A dermoscopic close-up of a skin lesion. A female subject approximately 35 years of age:
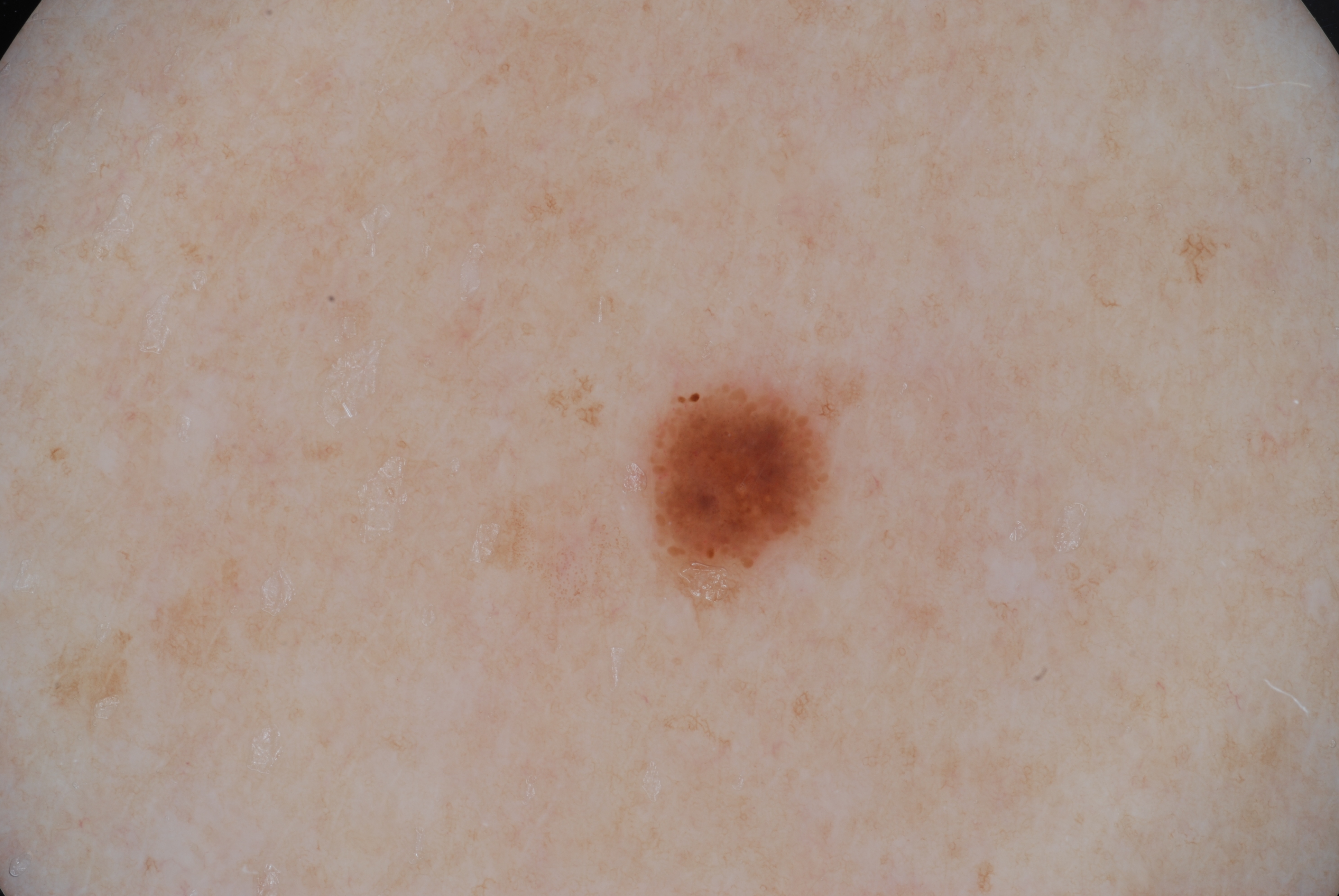- lesion location — left=641, top=383, right=828, bottom=574
- absent dermoscopic features — negative network, milia-like cysts, streaks, and pigment network
- lesion size — ~2% of the field
- diagnostic label — a melanocytic nevus, a benign lesion